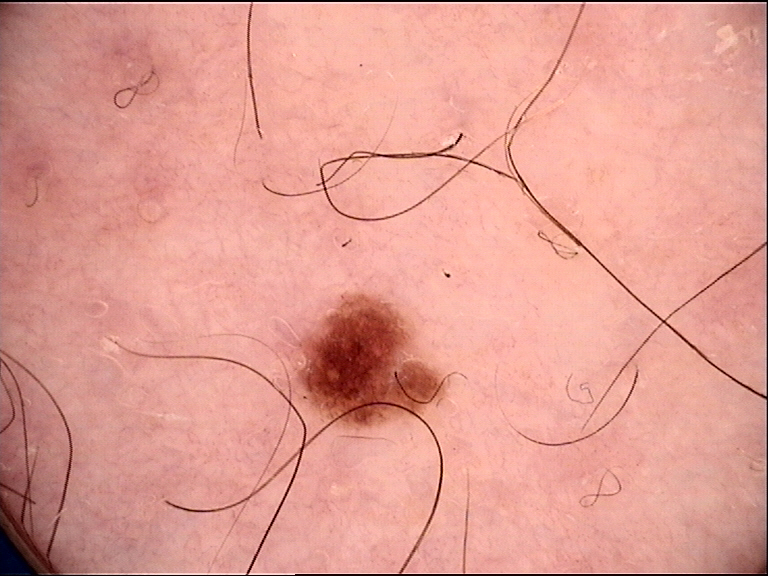diagnostic label: dysplastic junctional nevus (expert consensus).